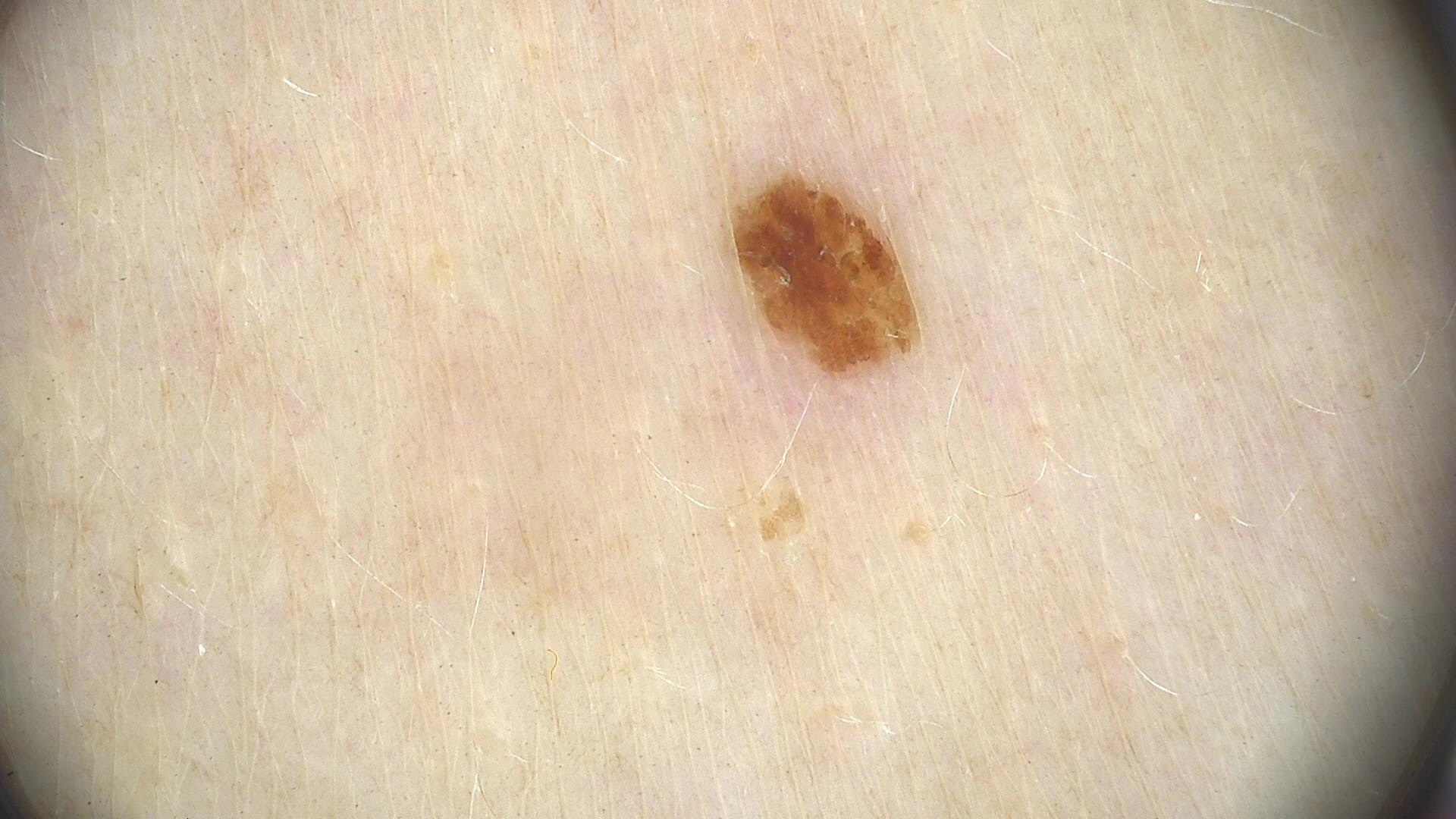<lesion>
<diagnosis>
<name>seborrheic keratosis</name>
<code>sk</code>
<malignancy>benign</malignancy>
<super_class>non-melanocytic</super_class>
<confirmation>expert consensus</confirmation>
</diagnosis>
</lesion>